A skin lesion imaged with a dermatoscope.
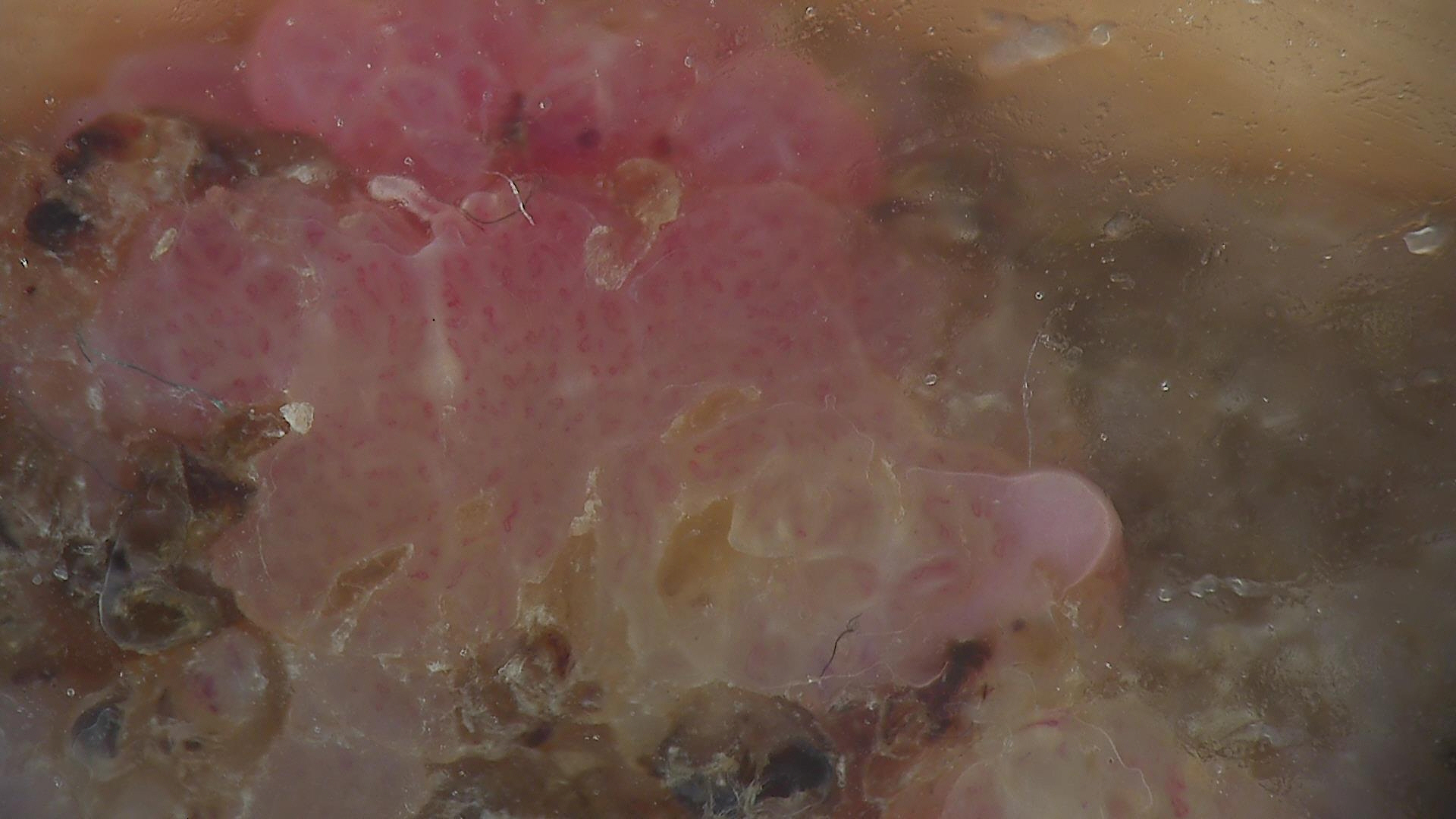Histopathologically confirmed as a malignant, keratinocytic lesion — a squamous cell carcinoma.